Skin tone: lay reviewers estimated Monk Skin Tone 2 or 3. The photograph was taken at an angle.
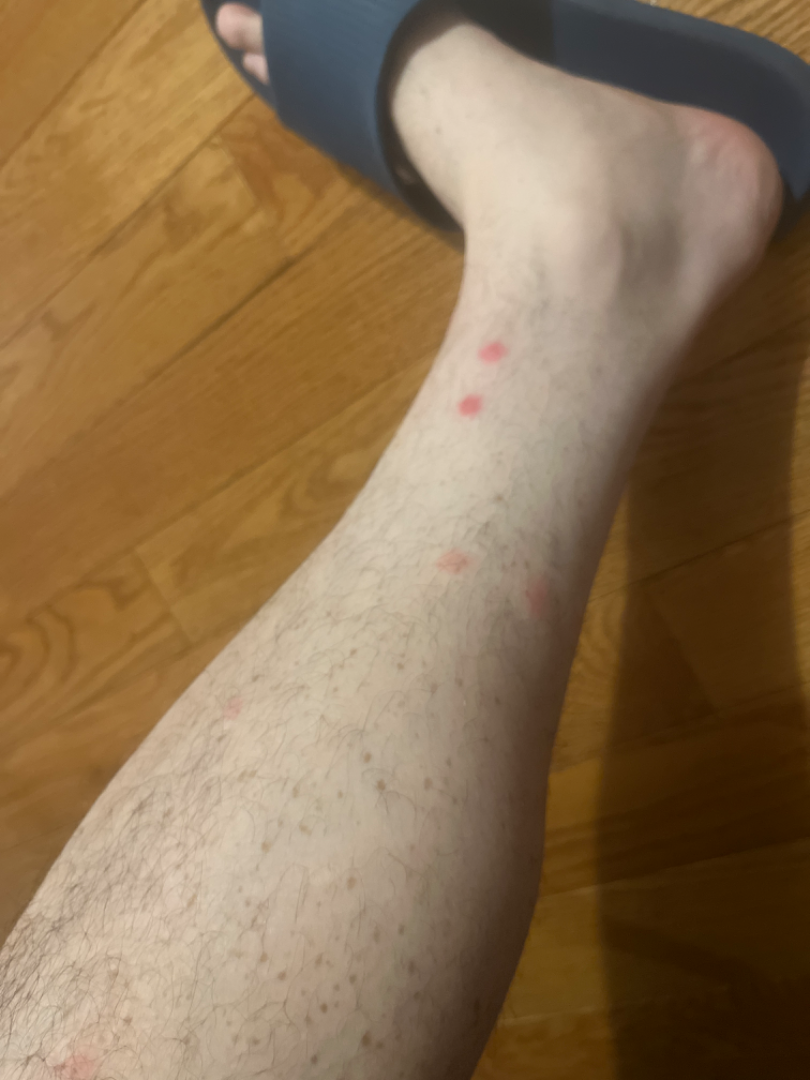The image was not sufficient for the reviewer to characterize the skin condition.